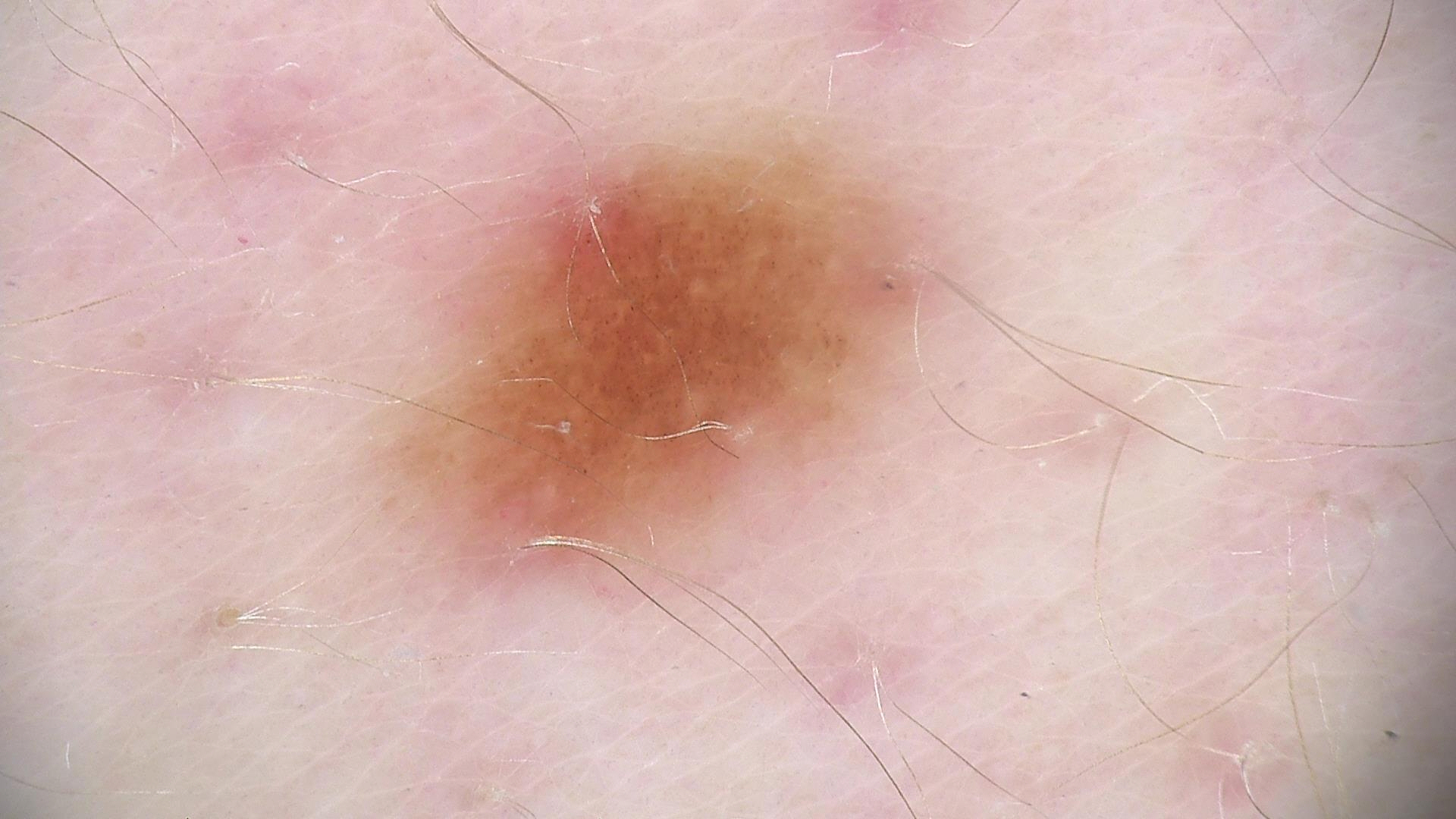image: dermoscopy; label: dysplastic junctional nevus (expert consensus).